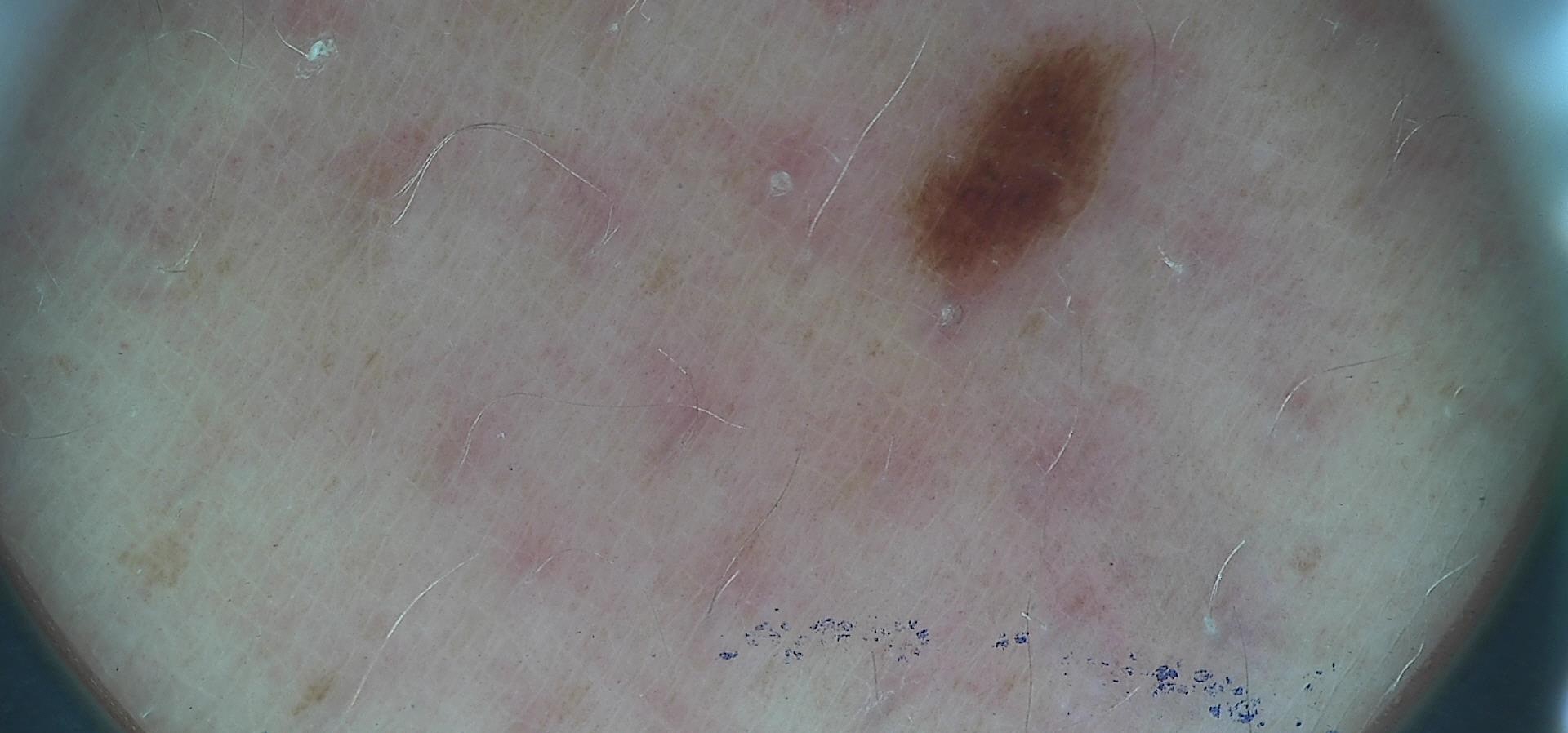Case: A dermoscopic image of a skin lesion. Conclusion: The diagnosis was a banal lesion — a junctional nevus.